A clinical photograph showing a skin lesion · a patient aged 75 — 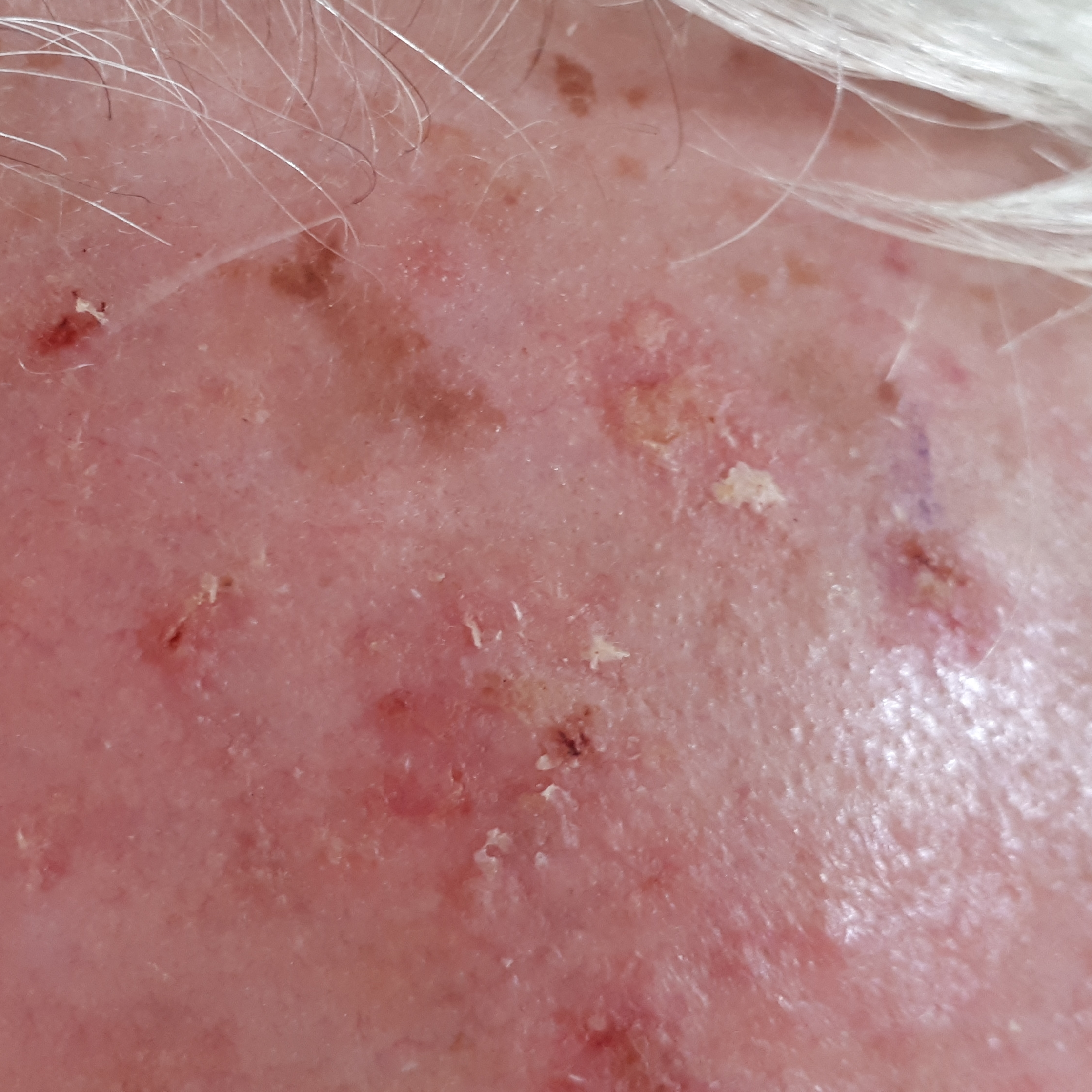Case summary: The lesion is on the face. The patient describes that the lesion has bled and itches. Impression: Diagnosed by dermatologist consensus as an actinic keratosis.